A macroscopic clinical photograph of a skin lesion. A male subject aged 79. Imaged for a research study, with no referral diagnosis recorded. Few moles overall by the patient's own estimate. The patient says their skin tans without first burning. The patient reports no immunosuppression: 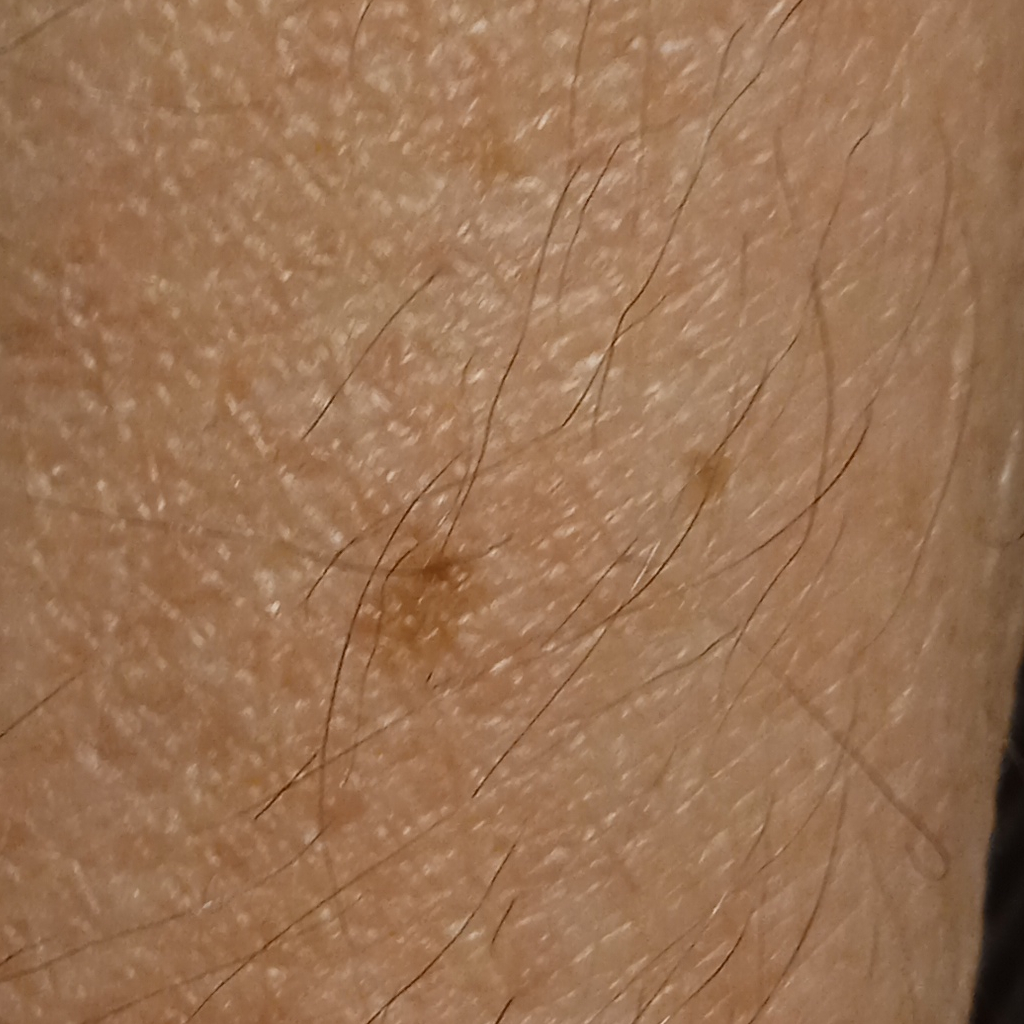Case:
* site — an arm
* diameter — 4.2 mm
* diagnostic label — seborrheic keratosis (dermatologist consensus)